No constitutional symptoms were reported, the lesion is associated with bothersome appearance, the photograph is a close-up of the affected area, the patient indicates the condition has been present for one to four weeks, the patient described the issue as acne: 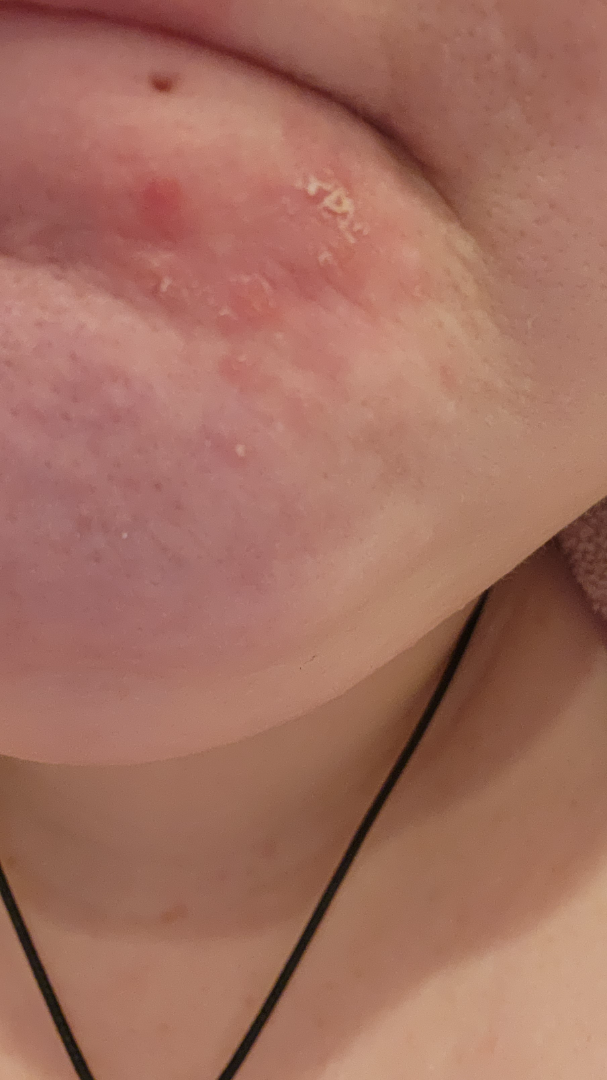Review: On teledermatology review, favoring Perioral Dermatitis; also raised was Impetigo; the differential also includes Irritant Contact Dermatitis.